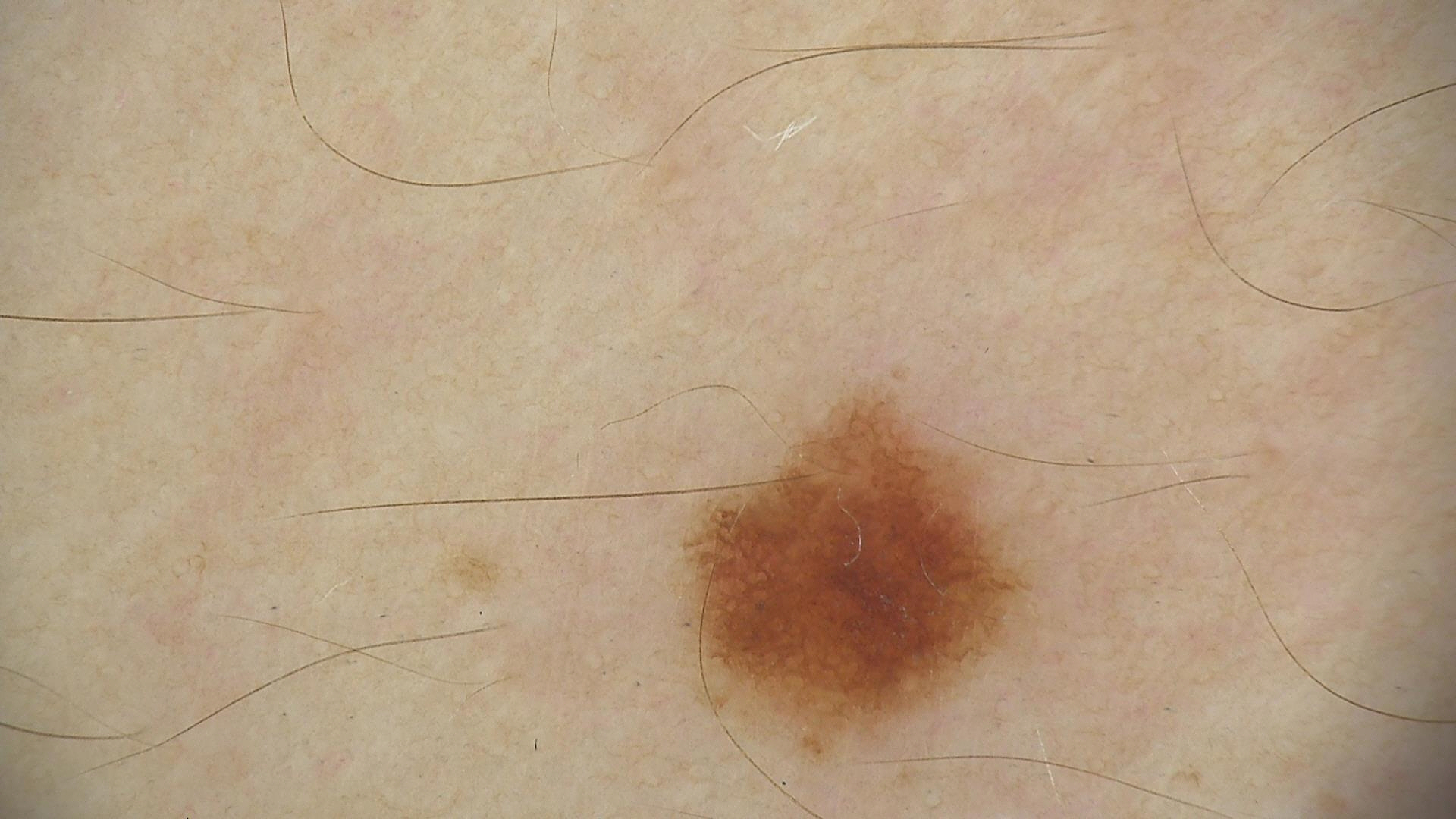{
  "image": "dermatoscopy",
  "lesion_type": {
    "main_class": "banal",
    "pattern": "junctional"
  },
  "diagnosis": {
    "name": "junctional nevus",
    "code": "jb",
    "malignancy": "benign",
    "super_class": "melanocytic",
    "confirmation": "expert consensus"
  }
}